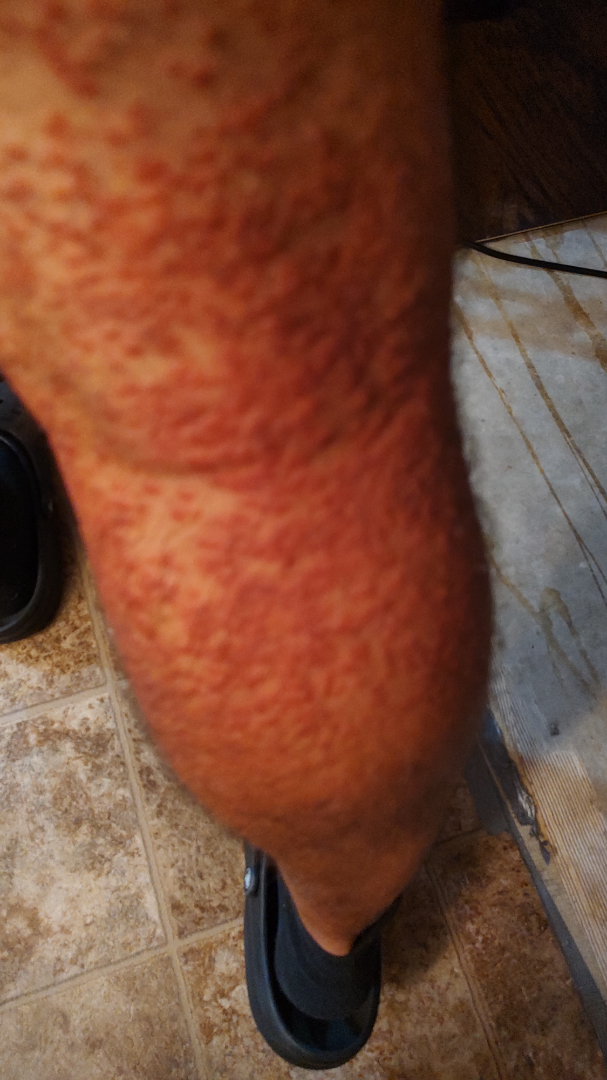An image taken at an angle.
Texture is reported as raised or bumpy and rough or flaky.
On dermatologist assessment of the image: most likely Lichen planus/lichenoid eruption; also raised was Hypersensitivity; lower on the differential is Eczema.